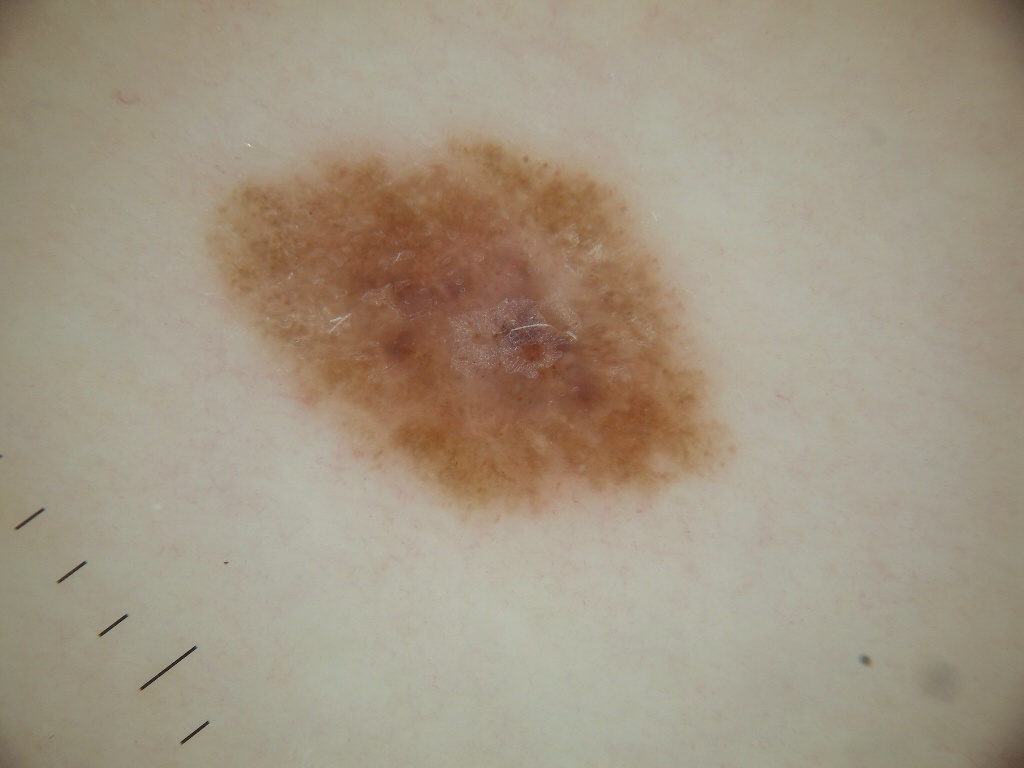A female patient in their mid-30s. A dermoscopic image of a skin lesion. On dermoscopy, the lesion shows negative network, with no streaks, pigment network, milia-like cysts, or globules. A moderately sized lesion. With coordinates (x1, y1, x2, y2), the lesion spans bbox(187, 129, 724, 515). The lesion was assessed as a melanocytic nevus.